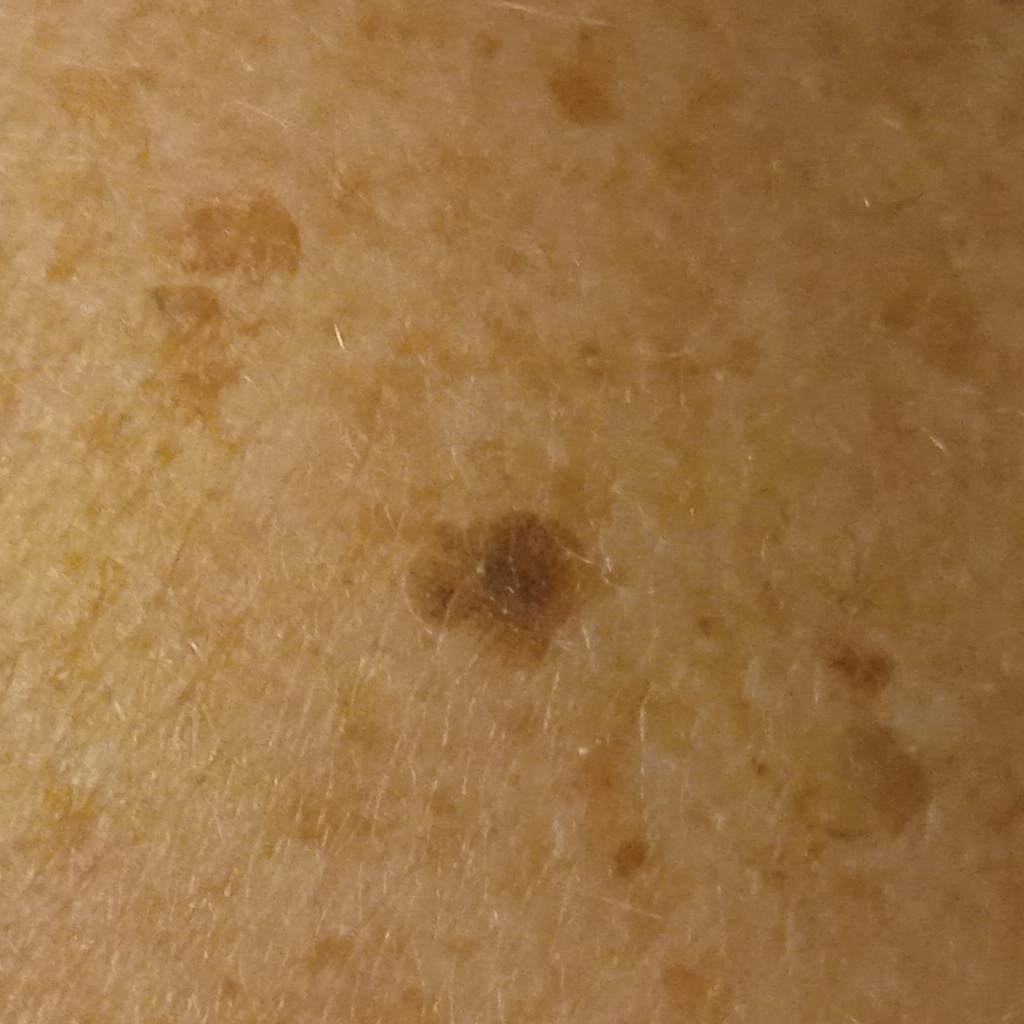patient: female, age 78
image type: clinical photograph
referral context: research study (no referral diagnosis)
body site: the back
lesion size: 5.6 mm
diagnosis: seborrheic keratosis (dermatologist consensus)